By history, prior malignancy (patient or family) and alcohol use. Recorded as Fitzpatrick phototype III:
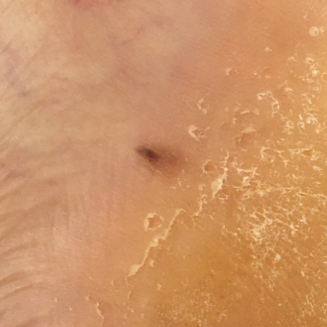Q: Any reported symptoms?
A: no bleeding, no elevation
Q: What is this lesion?
A: nevus (biopsy-proven)